A clinical photograph showing a skin lesion in context · a male subject aged approximately 65:
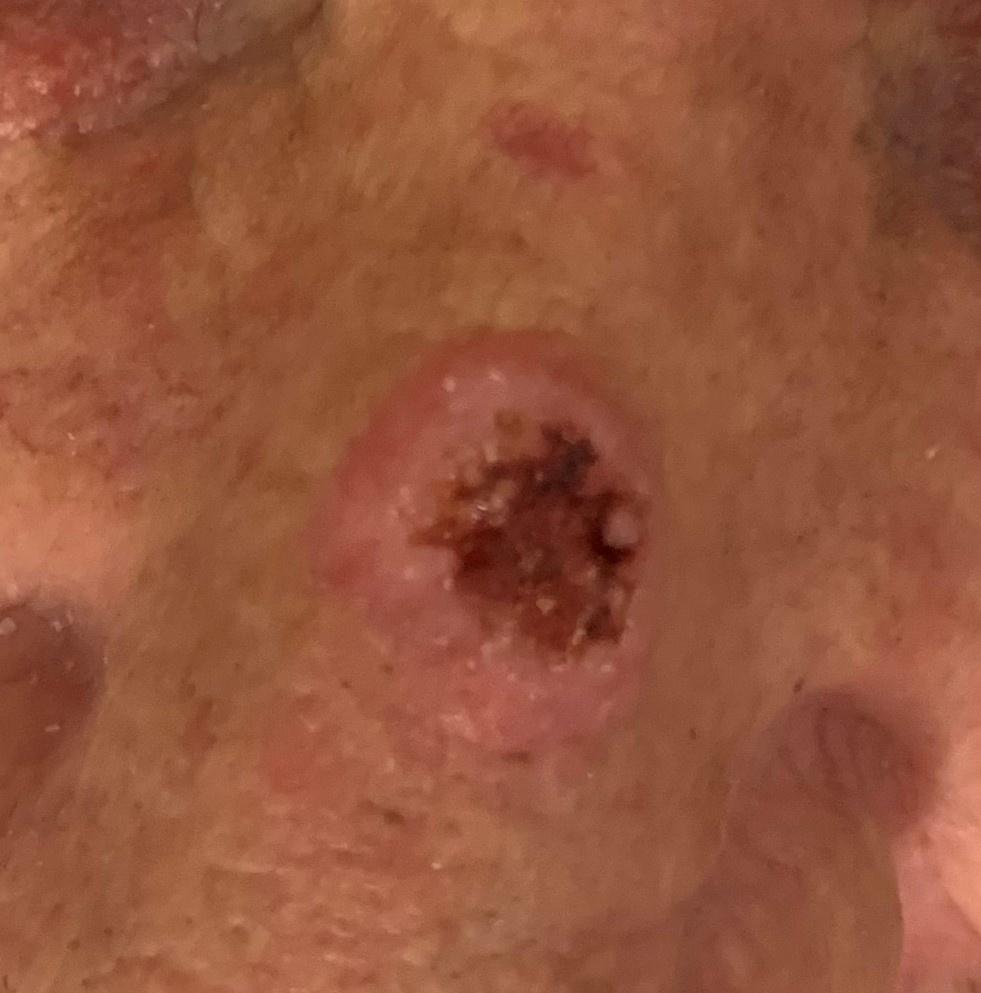site: the head or neck, diagnosis: Squamous cell carcinoma (biopsy-proven).